A skin lesion imaged with a dermatoscope.
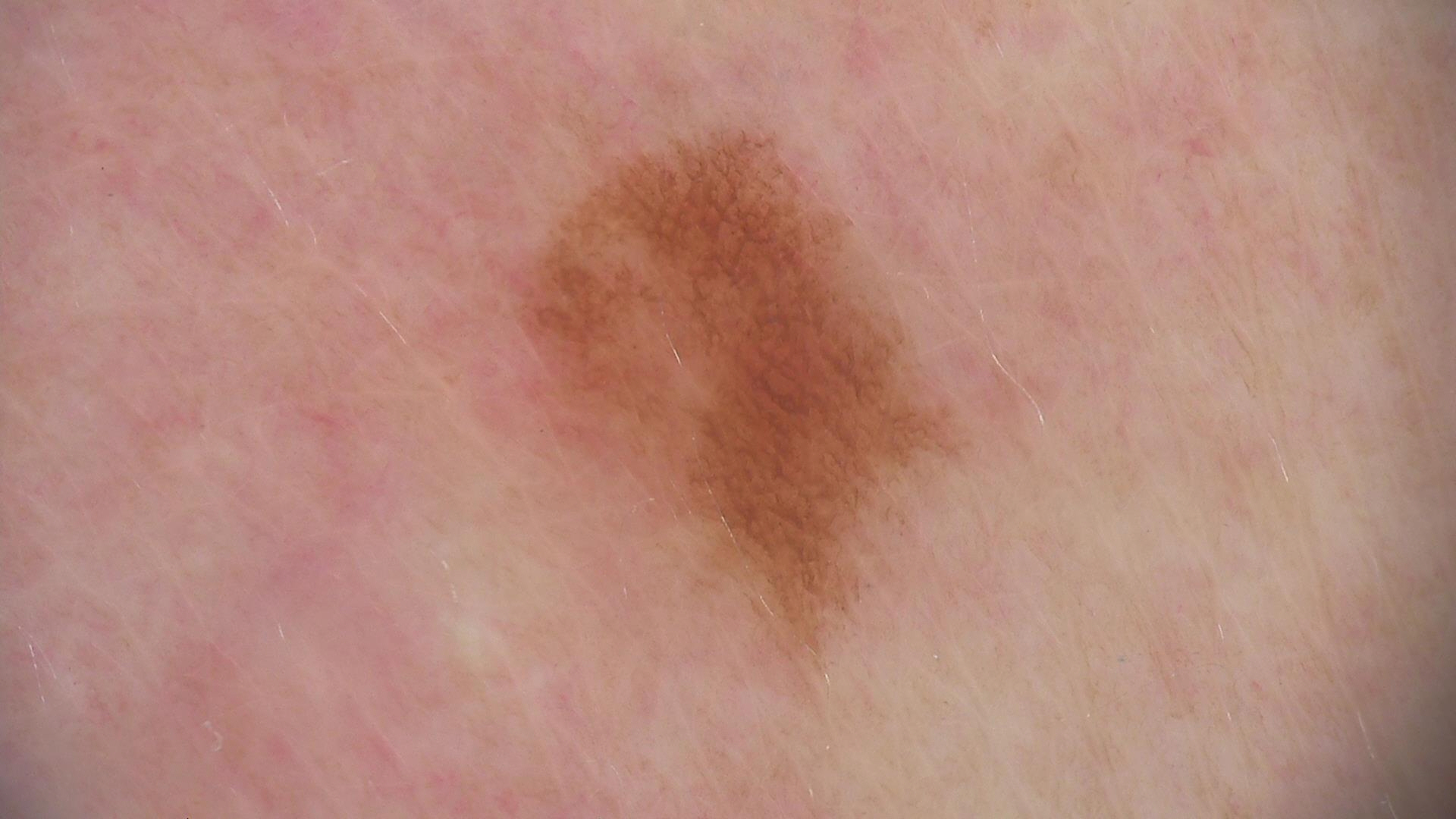{
  "diagnosis": {
    "name": "dysplastic junctional nevus",
    "code": "jd",
    "malignancy": "benign",
    "super_class": "melanocytic",
    "confirmation": "expert consensus"
  }
}